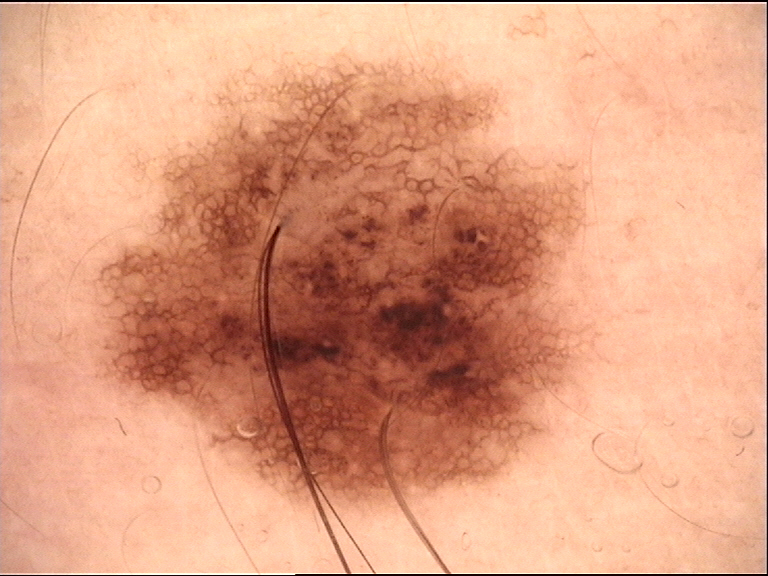A dermoscopic image of a skin lesion. Classified as a dysplastic compound nevus.